A dermoscopic image of a skin lesion:
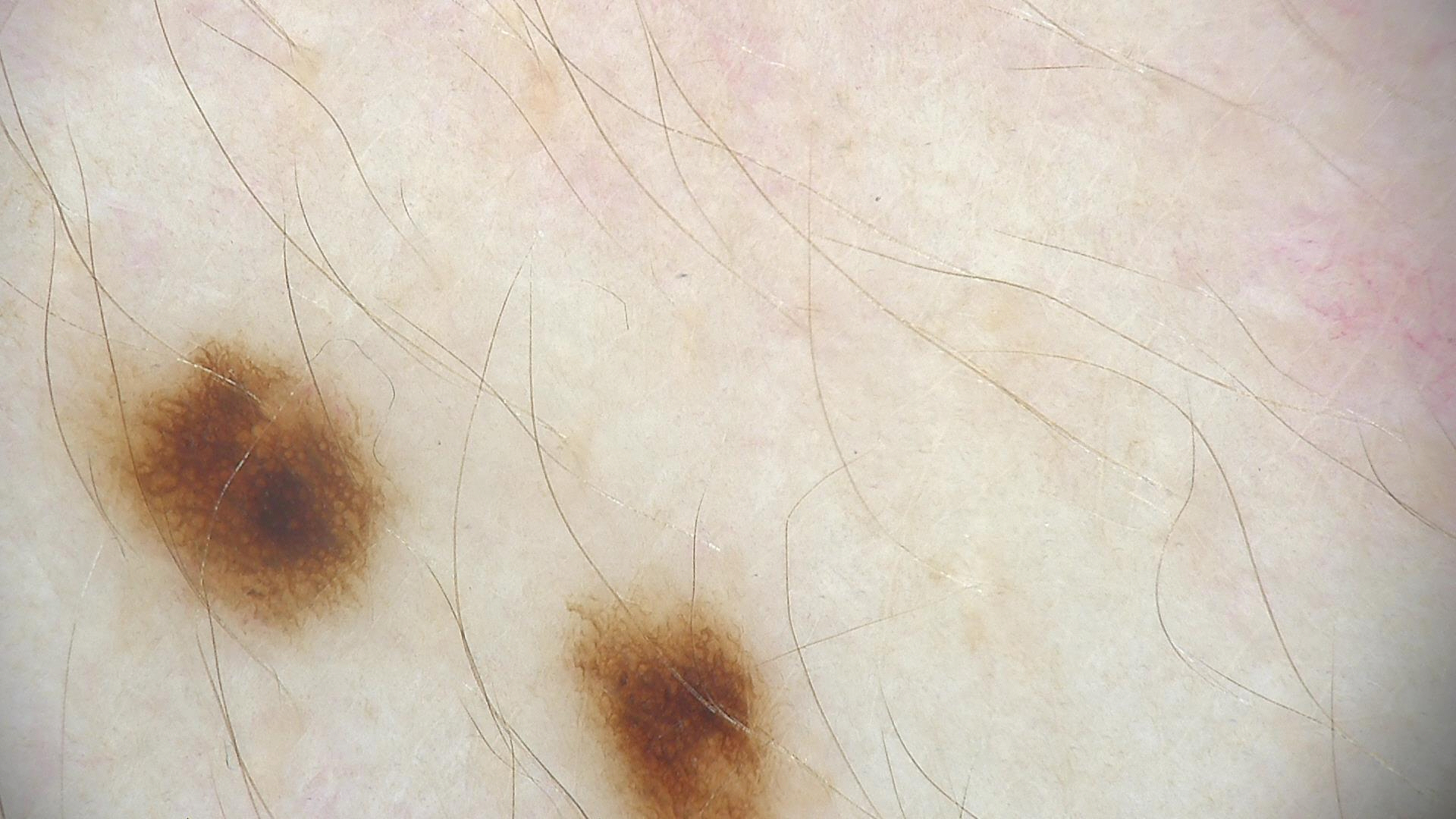{
  "diagnosis": {
    "name": "dysplastic junctional nevus",
    "code": "jd",
    "malignancy": "benign",
    "super_class": "melanocytic",
    "confirmation": "expert consensus"
  }
}